The patient is male. A close-up photograph. Located on the leg — 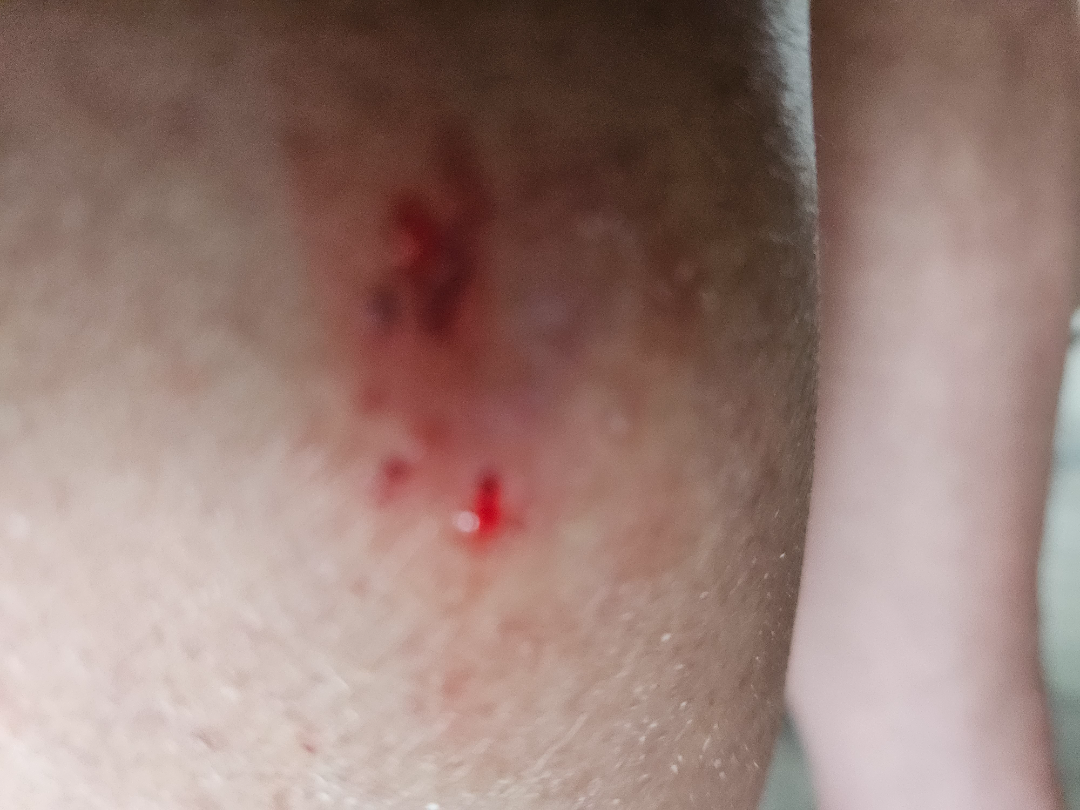Case summary:
* assessment · unable to determine
* reported symptoms · enlargement and itching
* described texture · flat
* self-categorized as · a rash
* duration · one to three months